A dermoscopy image of a single skin lesion.
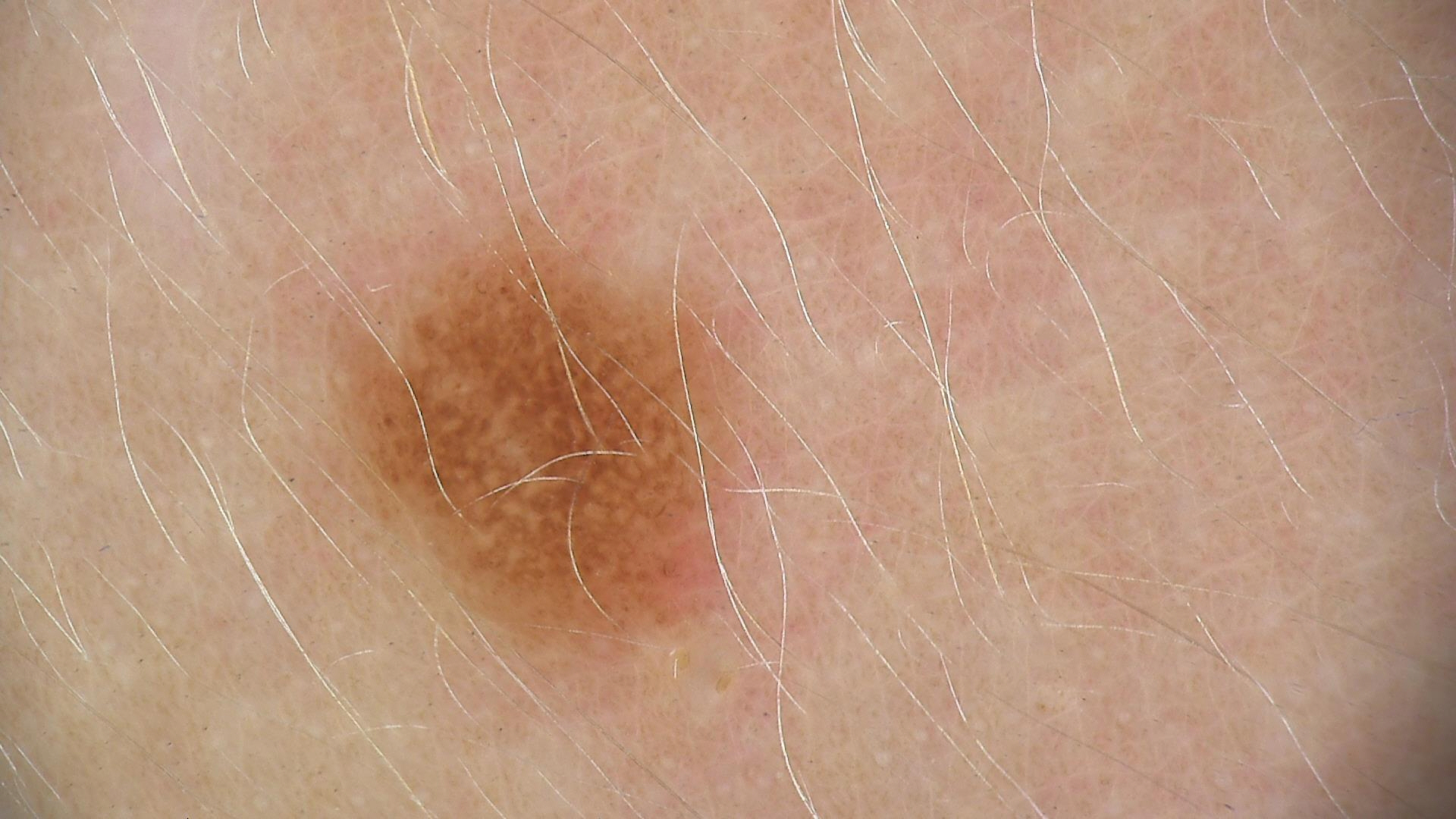label: dysplastic junctional nevus (expert consensus).